A dermoscopic photograph of a skin lesion:
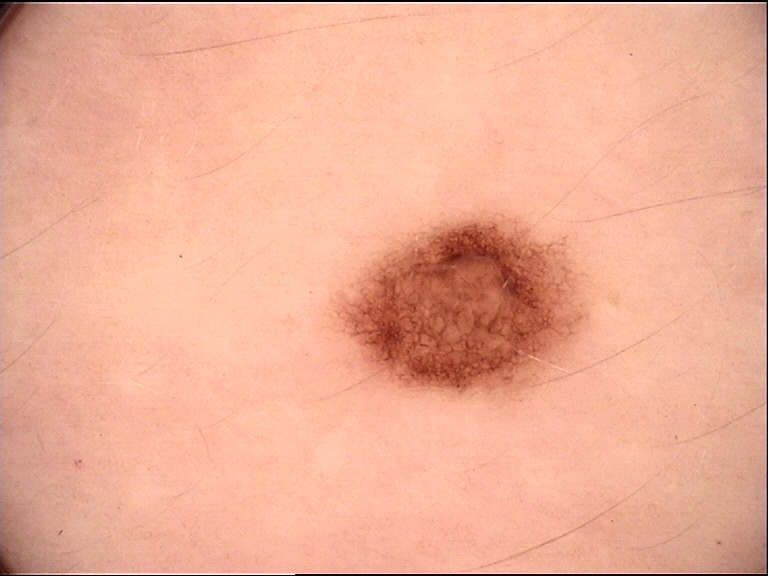The diagnostic label was a benign lesion — a dysplastic junctional nevus.